An image taken at a distance. The top or side of the foot is involved — 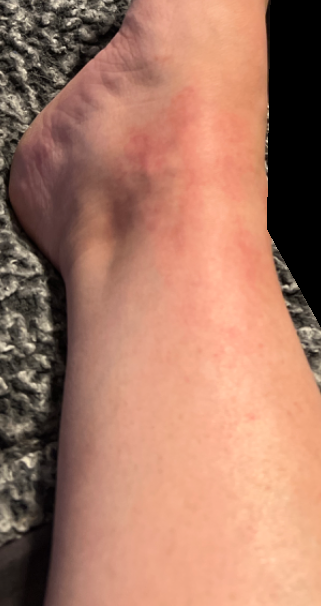Findings:
The skin findings could not be characterized from the image.
Background:
Reported lesion symptoms include darkening. Self-categorized by the patient as a rash. Reported duration is less than one week.